The photograph is a close-up of the affected area; the affected area is the front of the torso and arm: 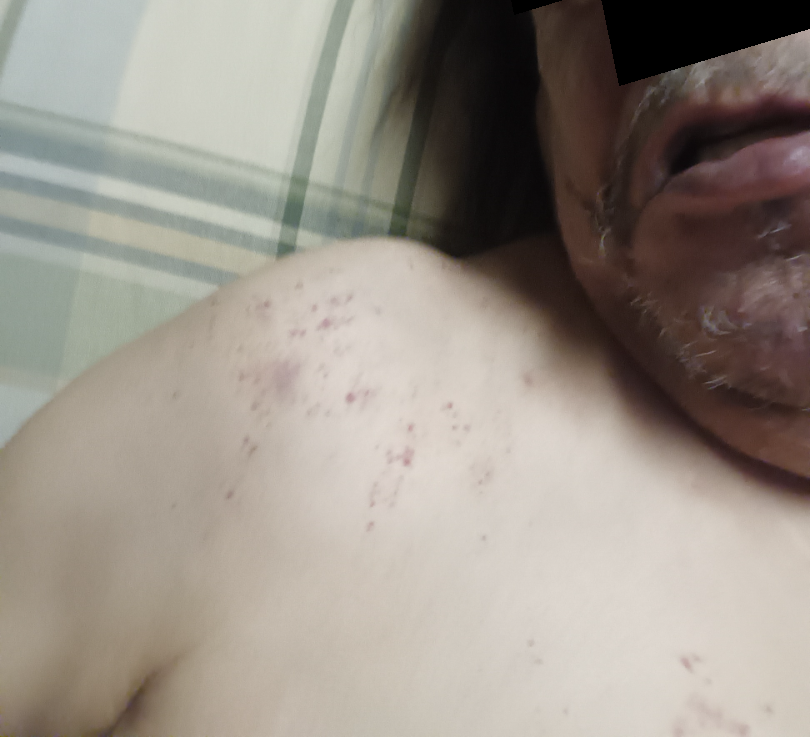{"assessment": "not assessable"}